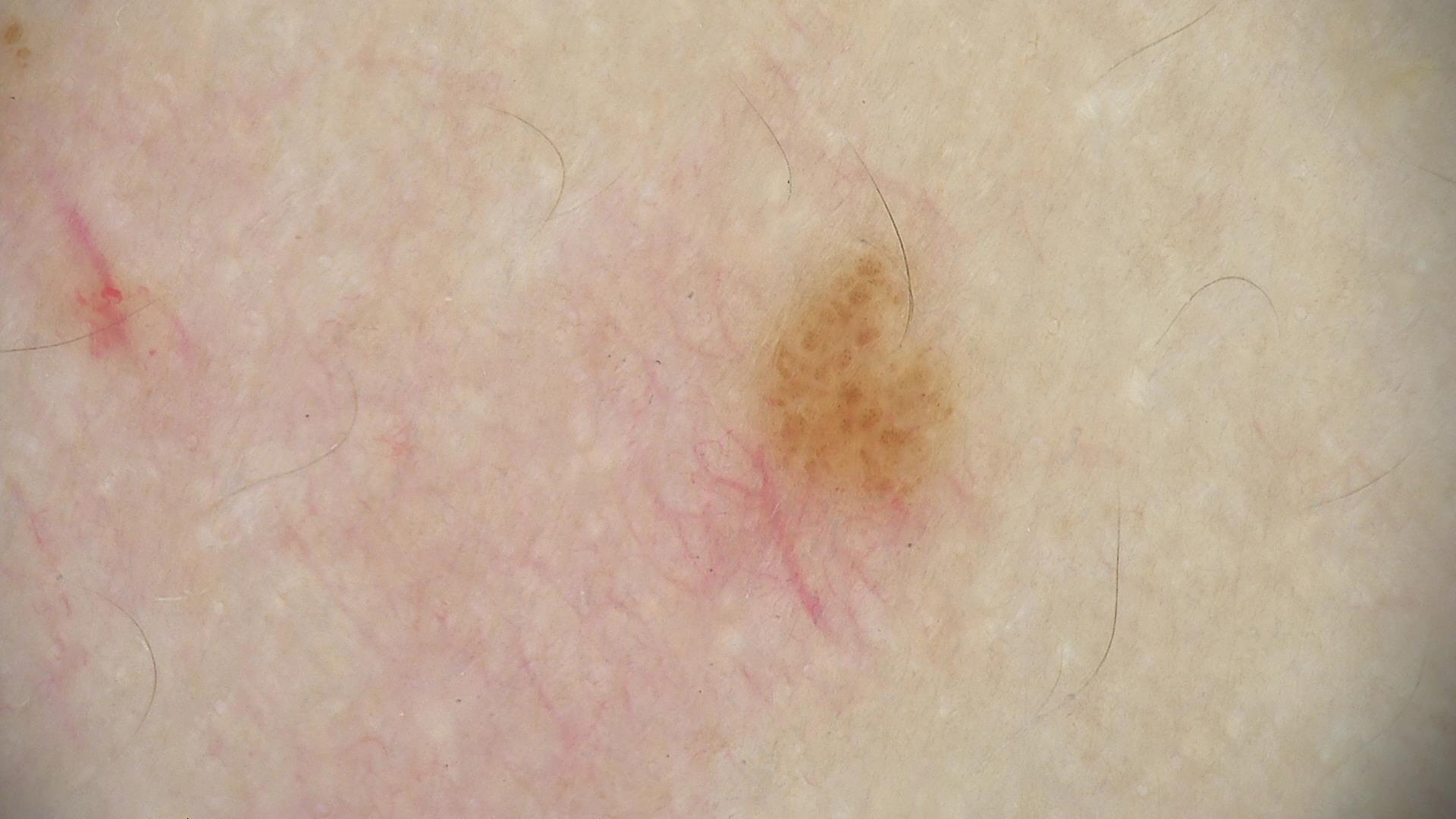A dermatoscopic image of a skin lesion. Labeled as a banal lesion — a junctional nevus.